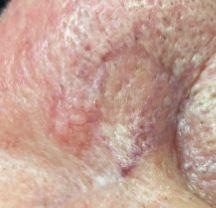{
  "lesion_location": {
    "region": "the head or neck"
  },
  "diagnosis": {
    "name": "Basal cell carcinoma",
    "malignancy": "malignant",
    "confirmation": "histopathology",
    "lineage": "adnexal"
  }
}